The photo was captured at an angle. The lesion involves the back of the torso. Female subject, age 18–29 — 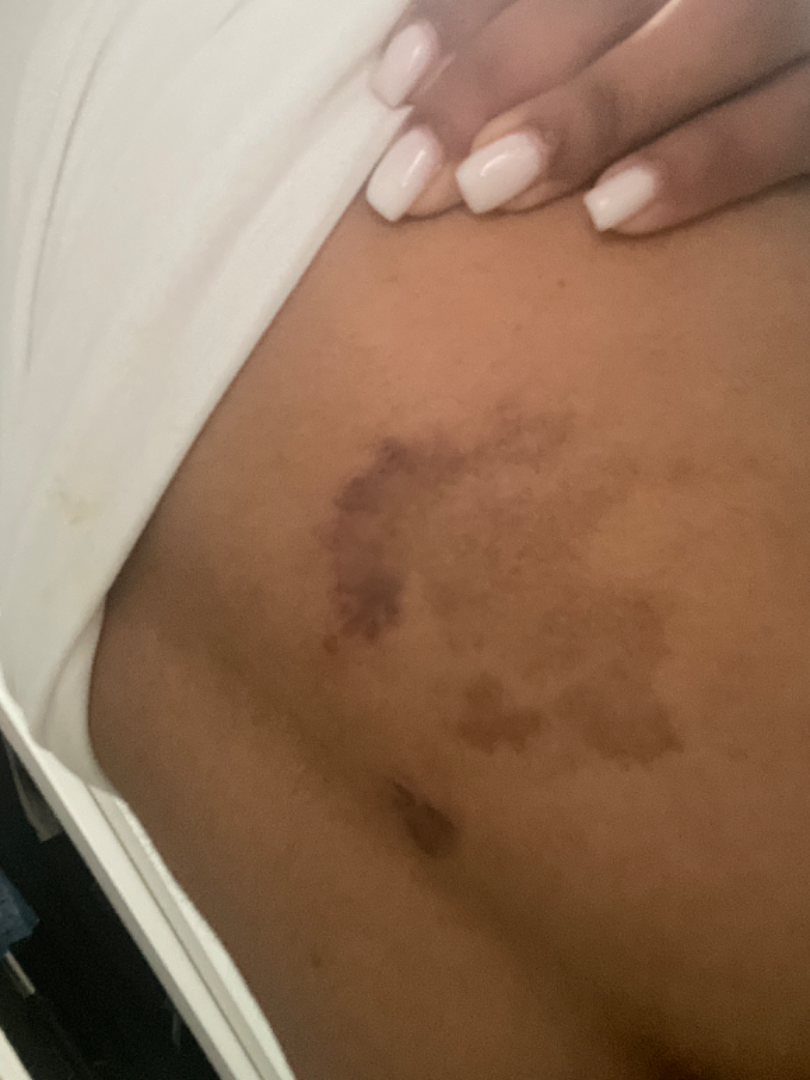  assessment: could not be assessed